A skin lesion imaged with a dermatoscope: 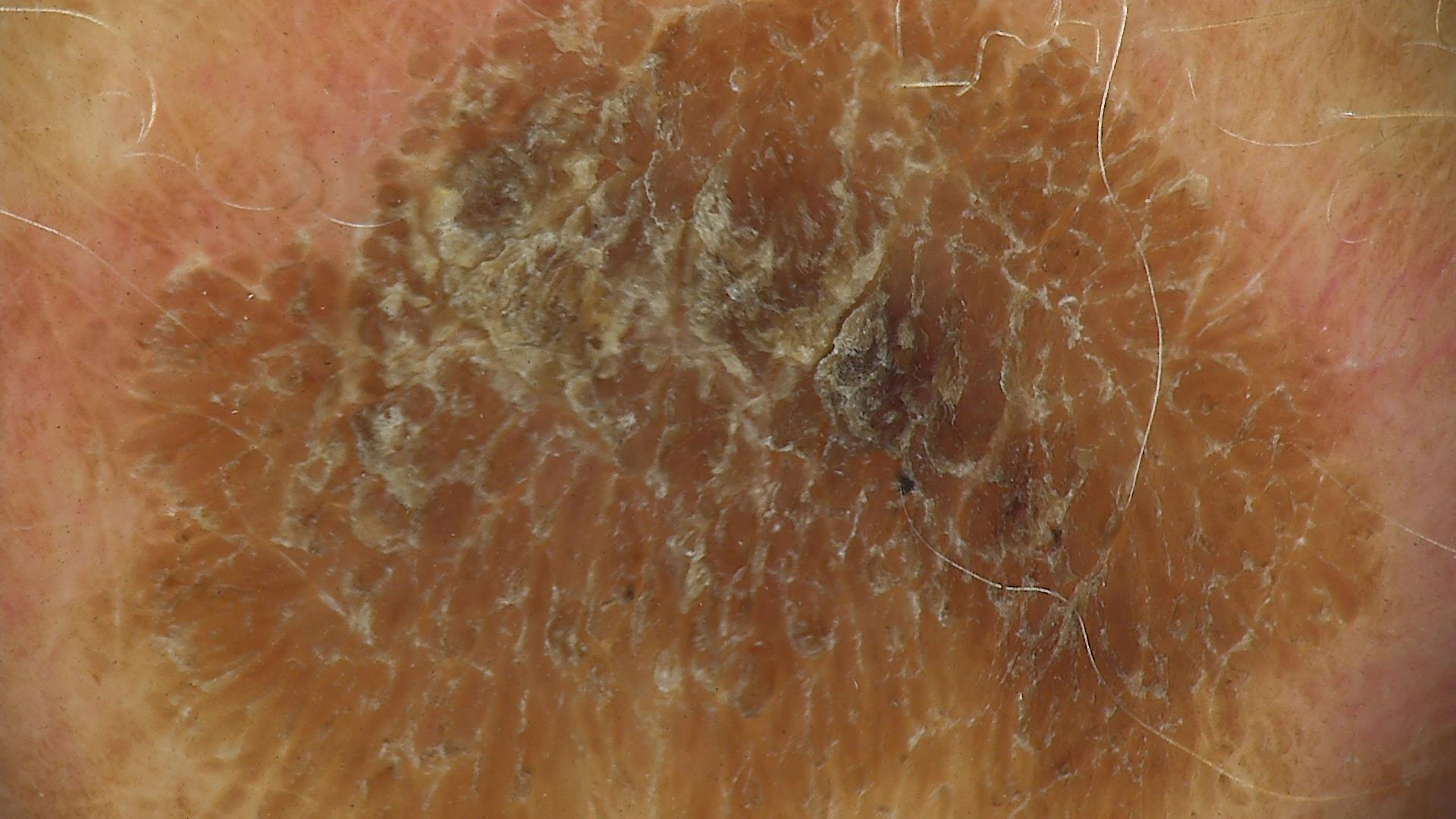- label: seborrheic keratosis (expert consensus)